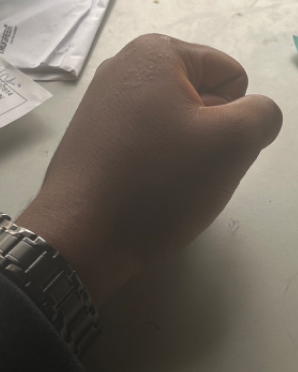  assessment: unable to determine
  shot_type: at a distance
  body_site: back of the hand
  systemic_symptoms: none reported
  symptoms: itching
  texture: raised or bumpy
  patient_category: a rash